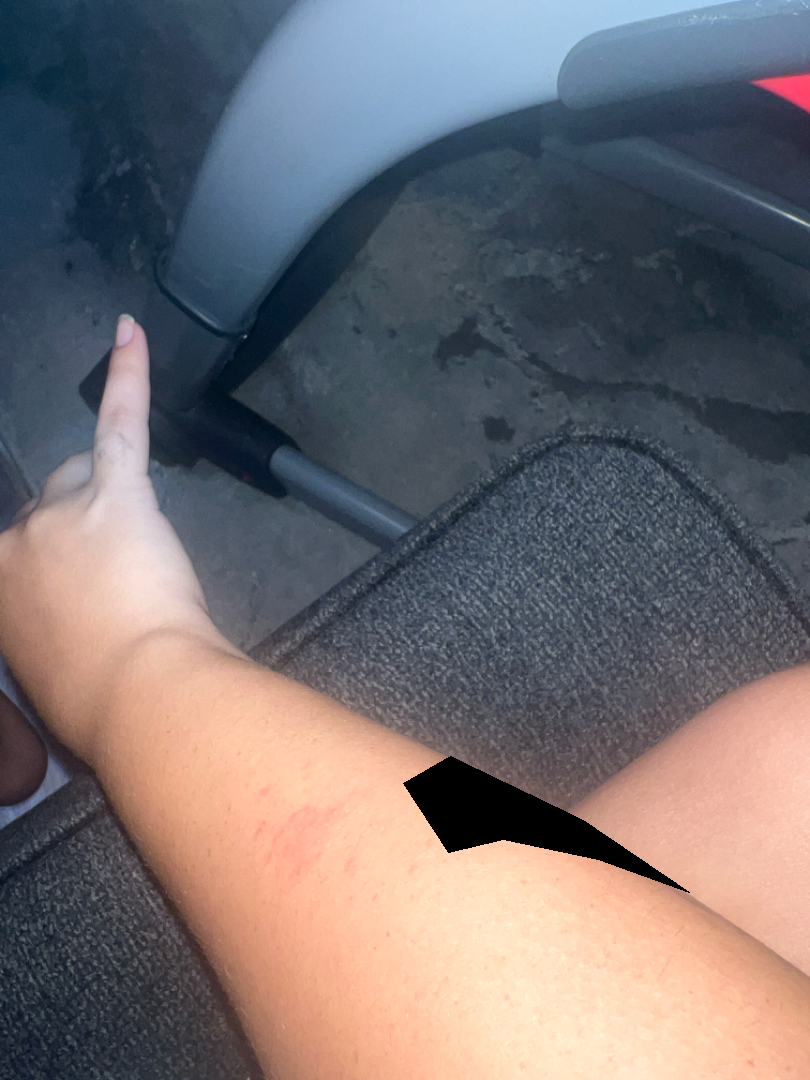Findings:
The image was not sufficient for the reviewer to characterize the skin condition.
Background:
The lesion involves the arm. Reported lesion symptoms include bothersome appearance. The photograph was taken at a distance. The lesion is described as raised or bumpy and fluid-filled.